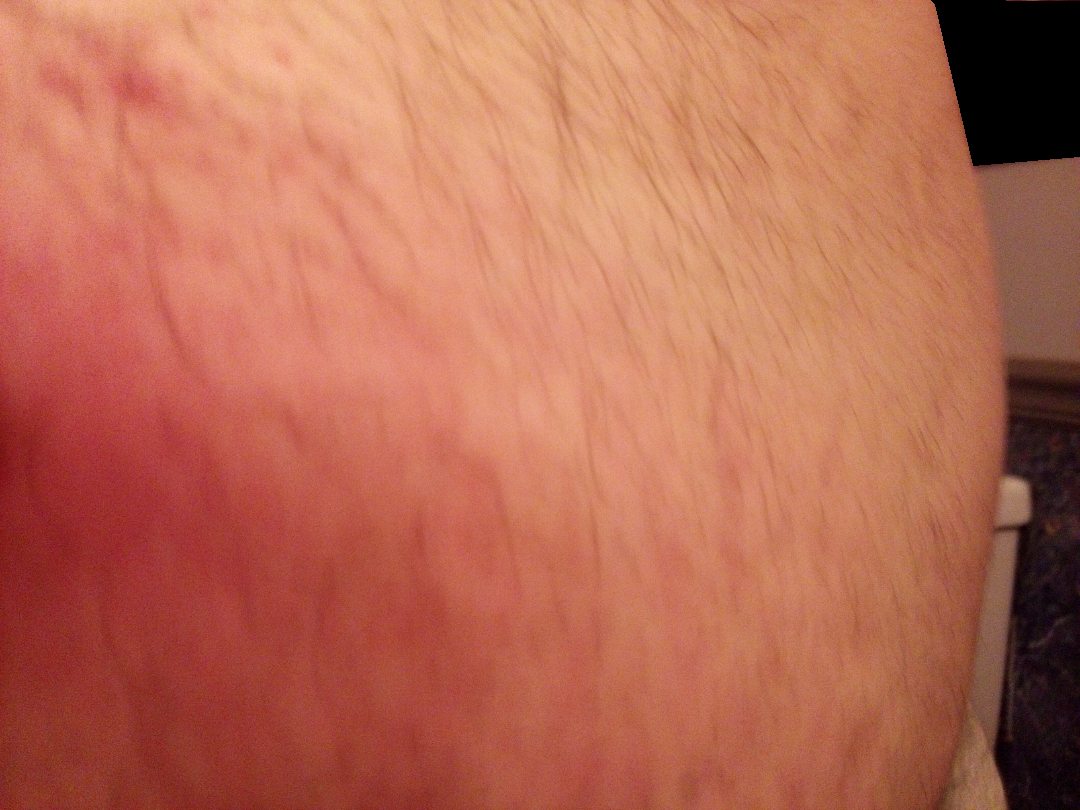Q: Could the case be diagnosed?
A: ungradable on photographic review